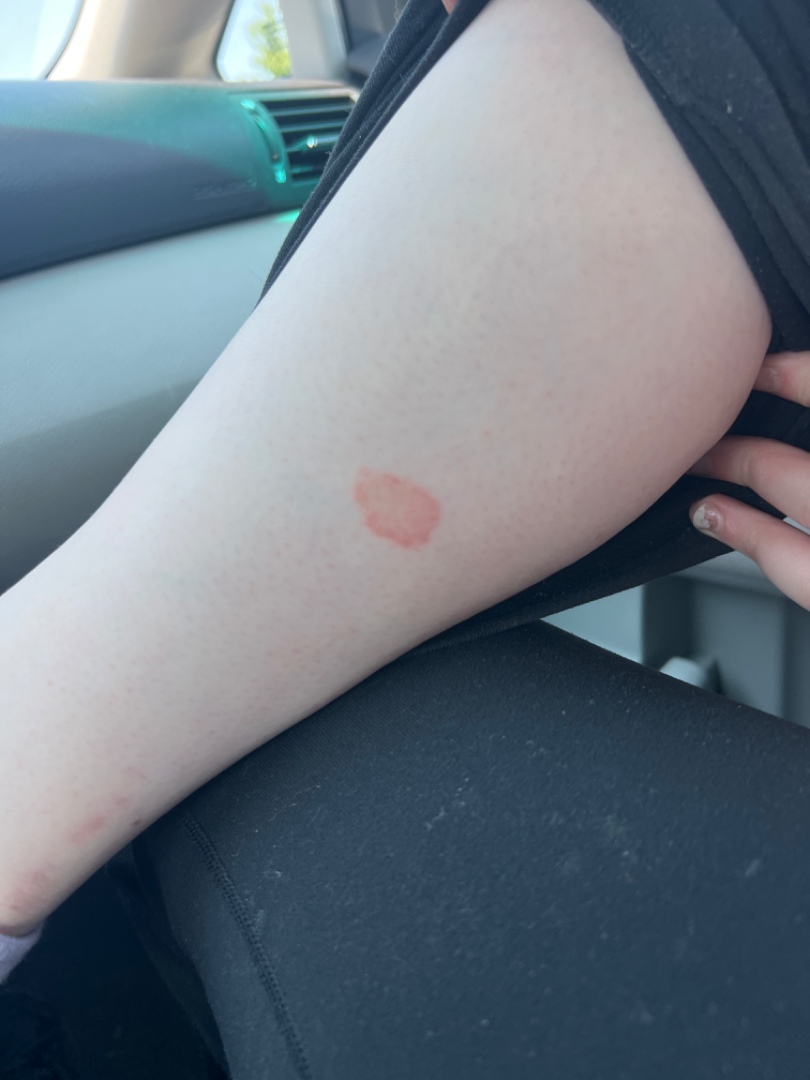clinical impression: the differential includes Eczema and Tinea, with no clear leading consideration; possibly Porokeratosis; less likely is Granuloma annulare.